This image was taken at an angle; the lesion involves the top or side of the foot:
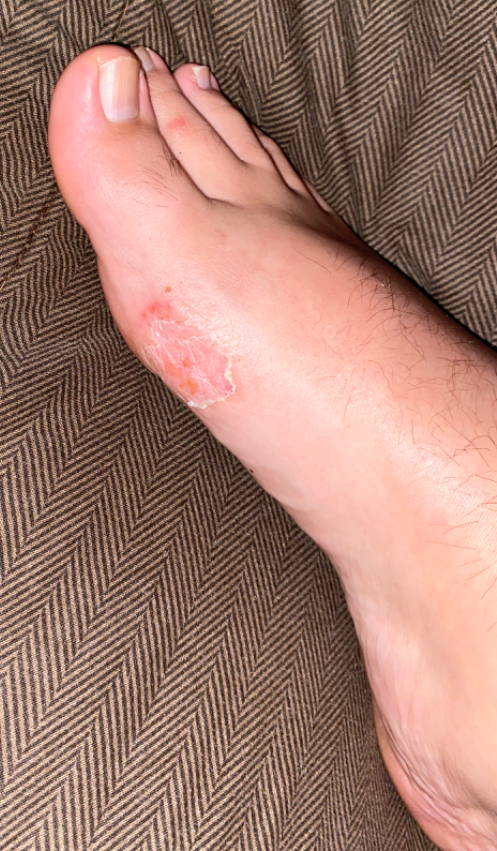The condition could not be reliably identified from the image.